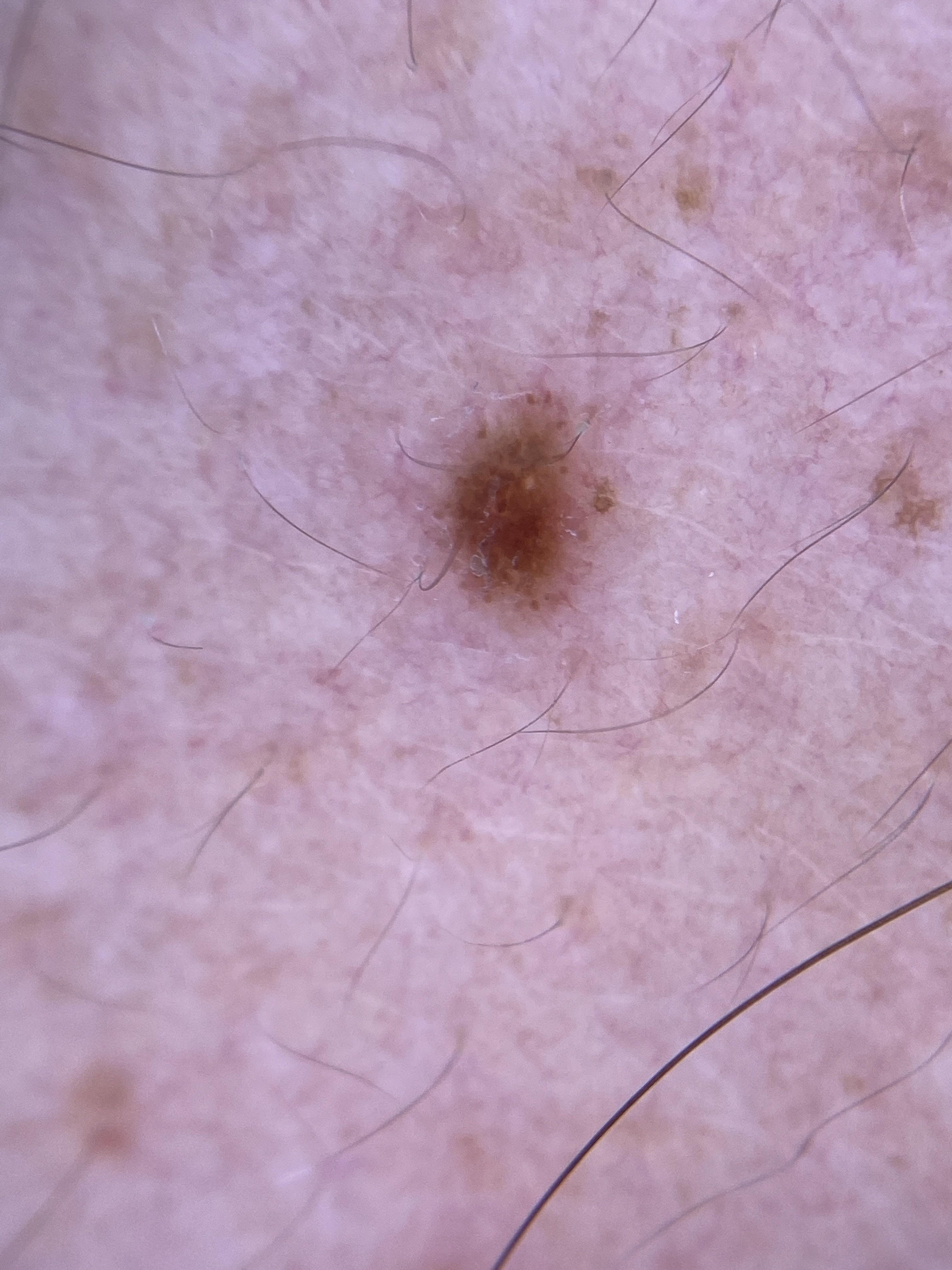imaging = dermoscopy; anatomic site = the trunk (the posterior trunk); pathology = Nevus (biopsy-proven).